A dermatoscopic image of a skin lesion.
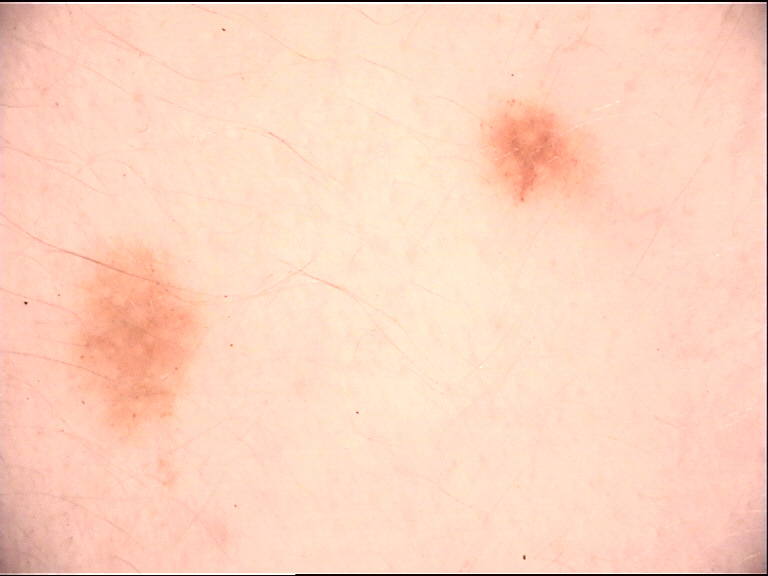Findings: The architecture is that of a banal lesion. Conclusion: Labeled as a compound nevus.